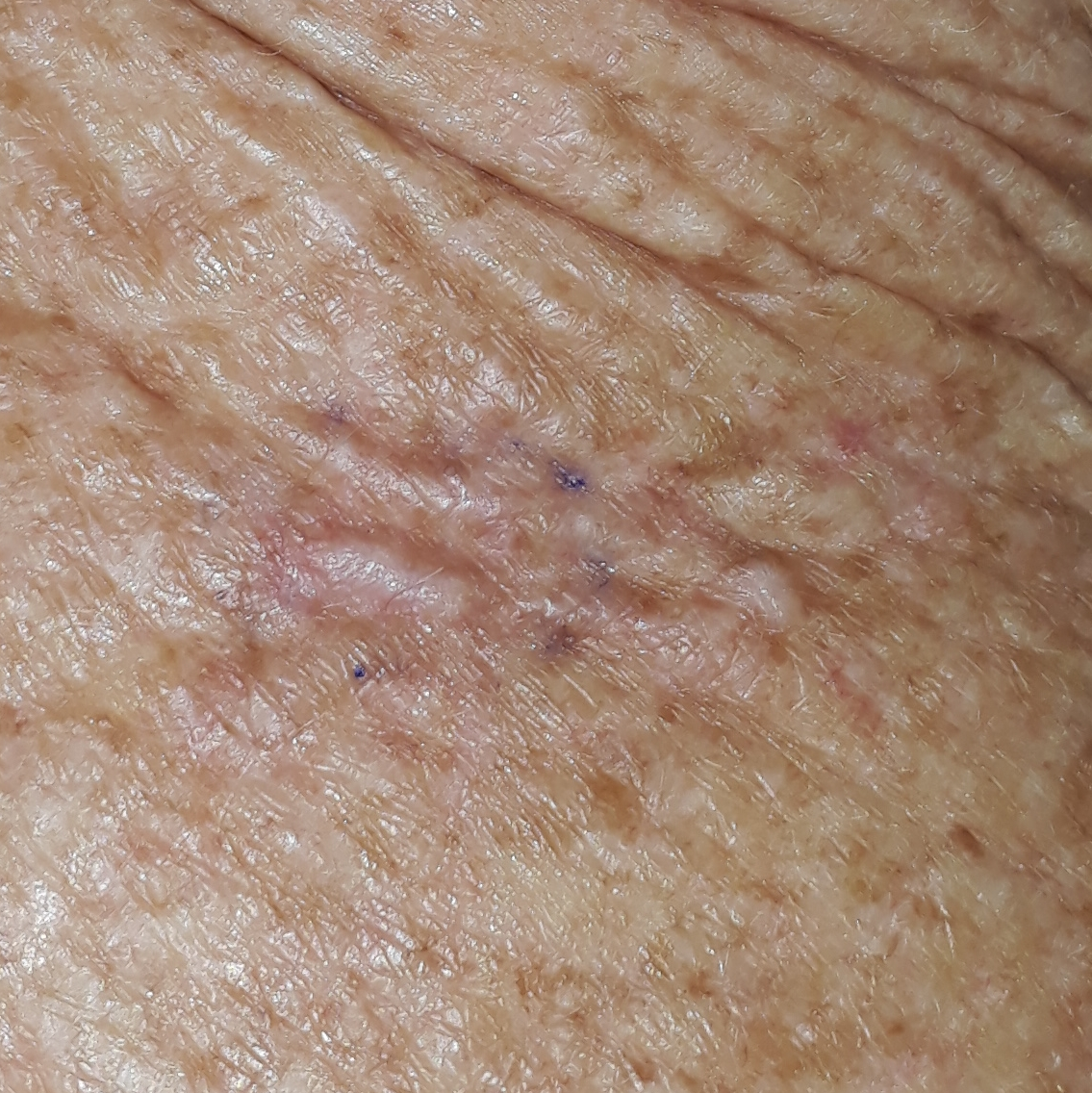Histopathology confirmed an actinic keratosis.